A skin lesion imaged with a dermatoscope. A male subject, approximately 80 years of age.
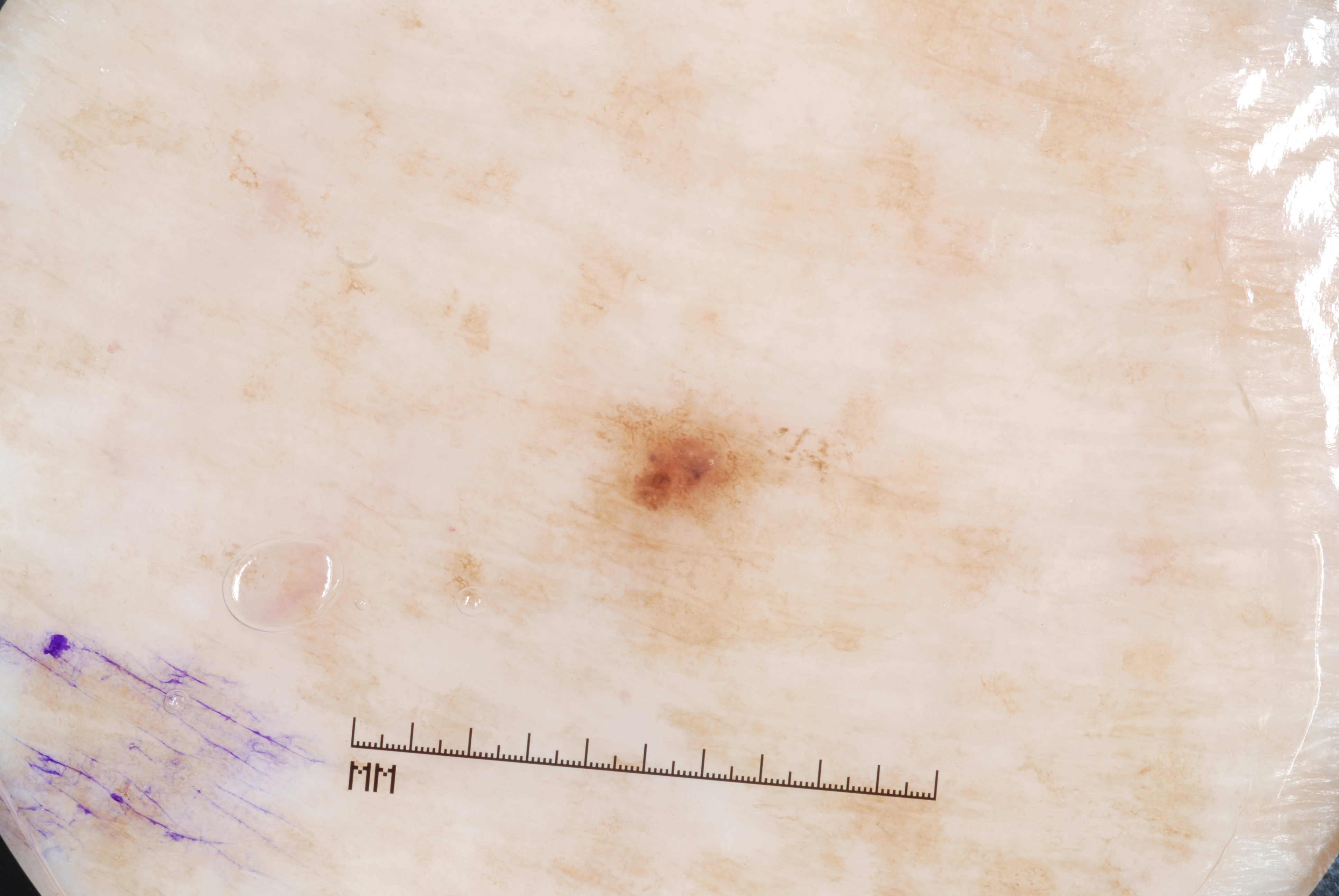Case summary:
– extent: moderate
– absent dermoscopic findings: pigment network, negative network, milia-like cysts, and streaks
– bounding box: <box>436, 370, 1039, 694</box>
– assessment: a melanocytic nevus, a benign skin lesion